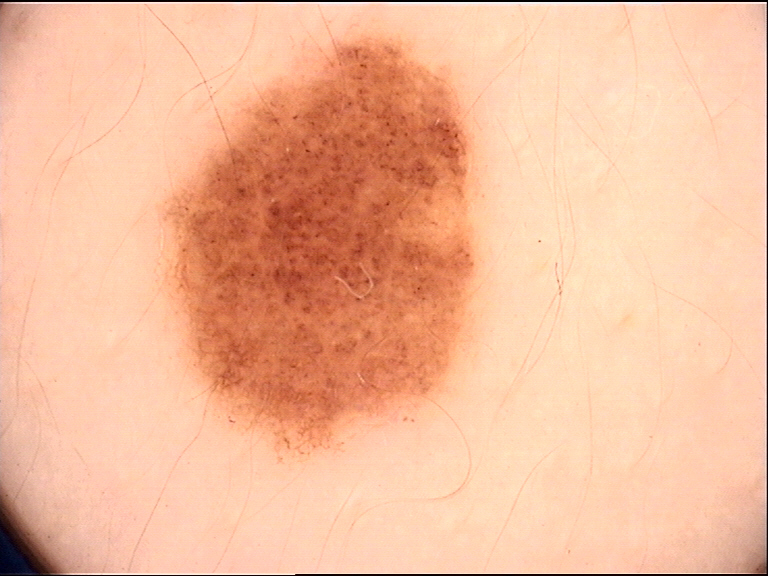Q: What was the diagnostic impression?
A: dysplastic junctional nevus (expert consensus)